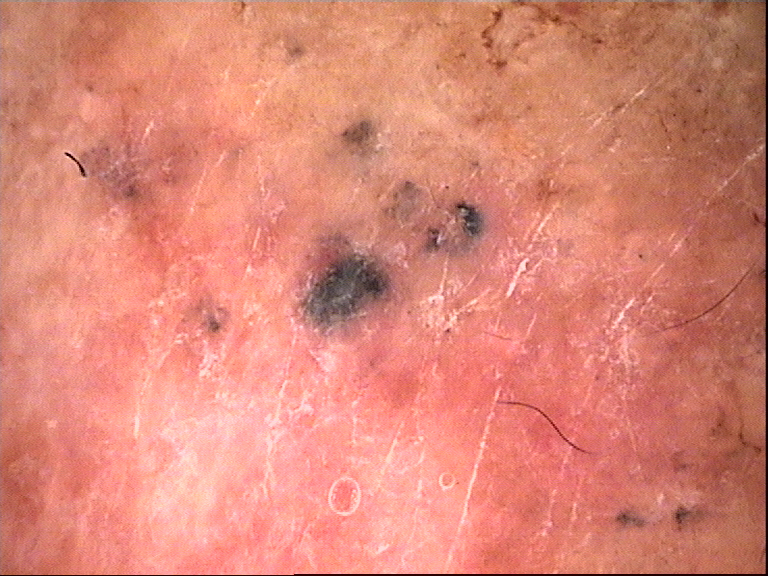Case: A dermoscopic close-up of a skin lesion. Diagnosis: Histopathology confirmed a basal cell carcinoma.